Dermoscopy of a skin lesion.
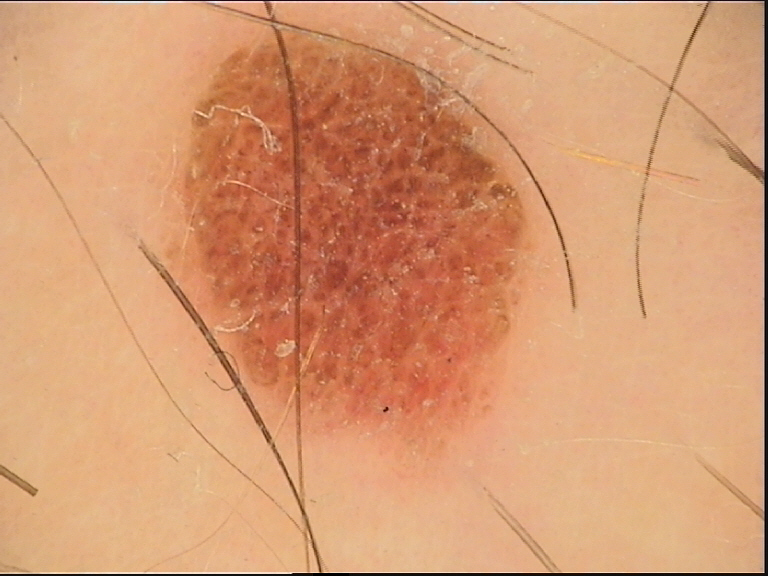Labeled as a compound nevus.